A close-up photograph, the top or side of the foot is involved — 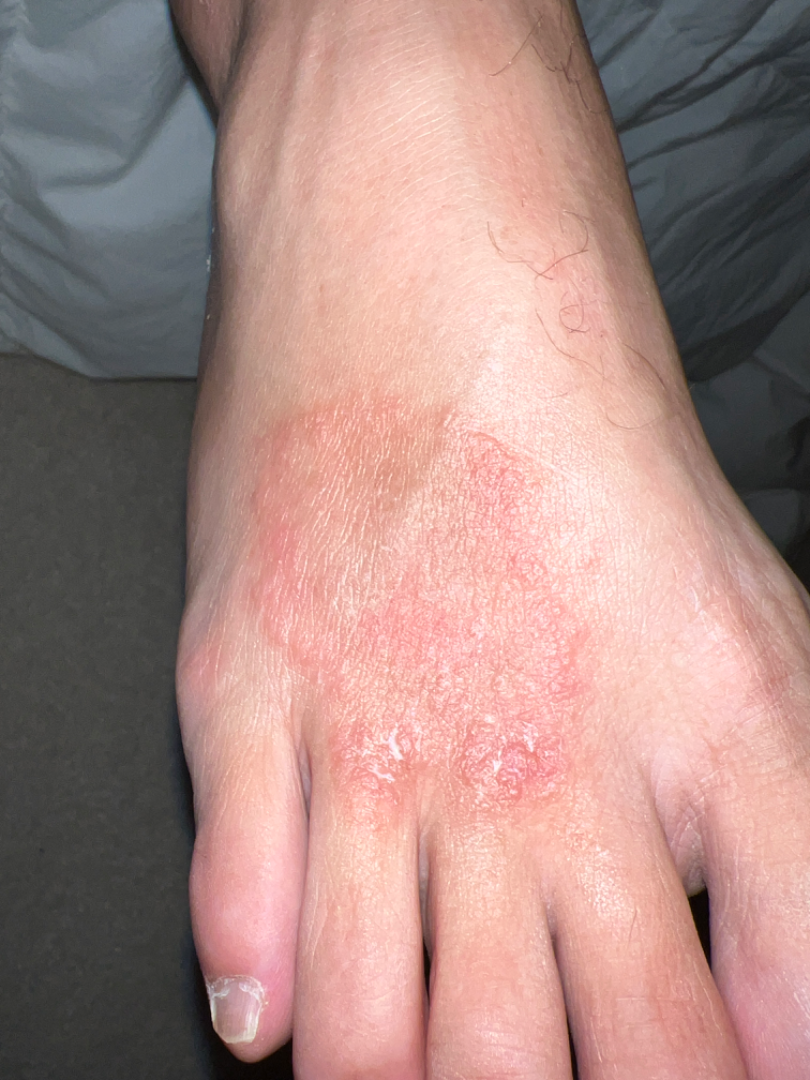surface texture — raised or bumpy
patient's own categorization — a rash
skin tone — Fitzpatrick I; non-clinician graders estimated MST 3 (US pool) or 2 (India pool)
onset — one to four weeks
lesion symptoms — none reported
constitutional symptoms — none reported
dermatologist impression — Tinea (primary); Psoriasis (possible); Eczema (possible)